Male subject, age 18–29. The lesion is described as flat. The lesion is associated with itching. Located on the arm. Present for about one day. The photograph is a close-up of the affected area:
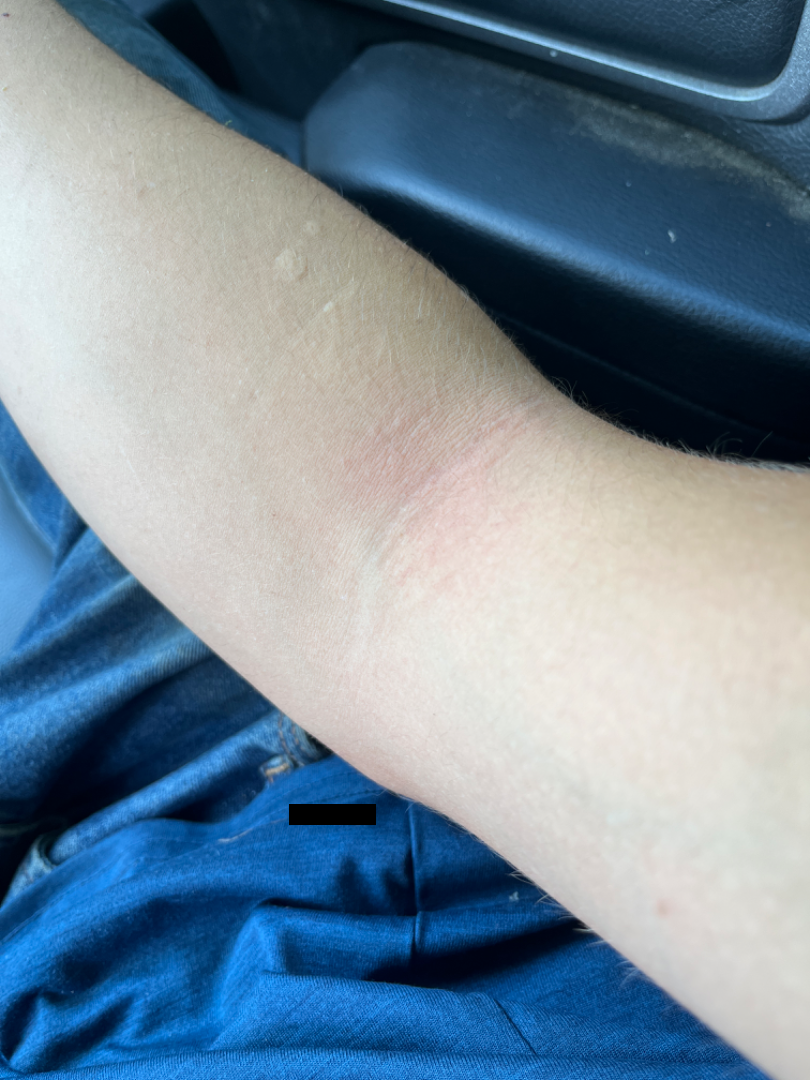Impression:
Reviewed remotely by one dermatologist: the favored diagnosis is Eczema; also raised was Irritant Contact Dermatitis.